Skin tone: human graders estimated MST 6 (US pool) or 4 (India pool). The affected area is the arm. The condition has been present for less than one week. Close-up view: 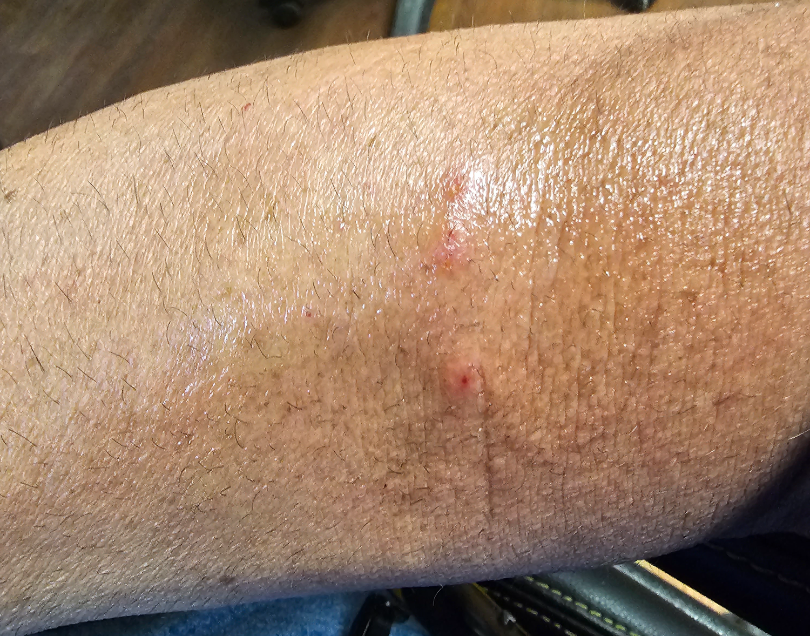Findings:
* impression: the differential is split between Impetigo and Allergic Contact Dermatitis